The patient is female · the patient notes associated fever and joint pain · the photograph was taken at an angle · located on the top or side of the foot · reported lesion symptoms include burning, enlargement, pain, bothersome appearance, itching and darkening · the patient notes the condition has been present for one to three months · Fitzpatrick III; lay graders estimated Monk Skin Tone 4 (US pool) or 2 (India pool) — 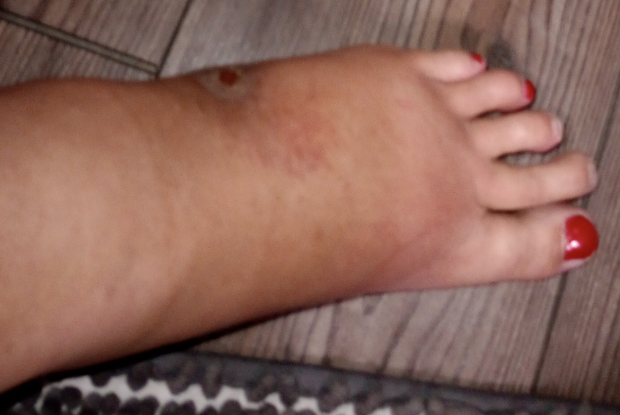On remote dermatologist review, the differential is split between Foot ulcer and Stasis Dermatitis; also raised was Leukocytoclastic Vasculitis.